A dermatoscopic image of a skin lesion; imaged for a research study, with no referral diagnosis recorded; few moles overall by the patient's own estimate; by self-report, no sunbed use; a female patient 67 years old:
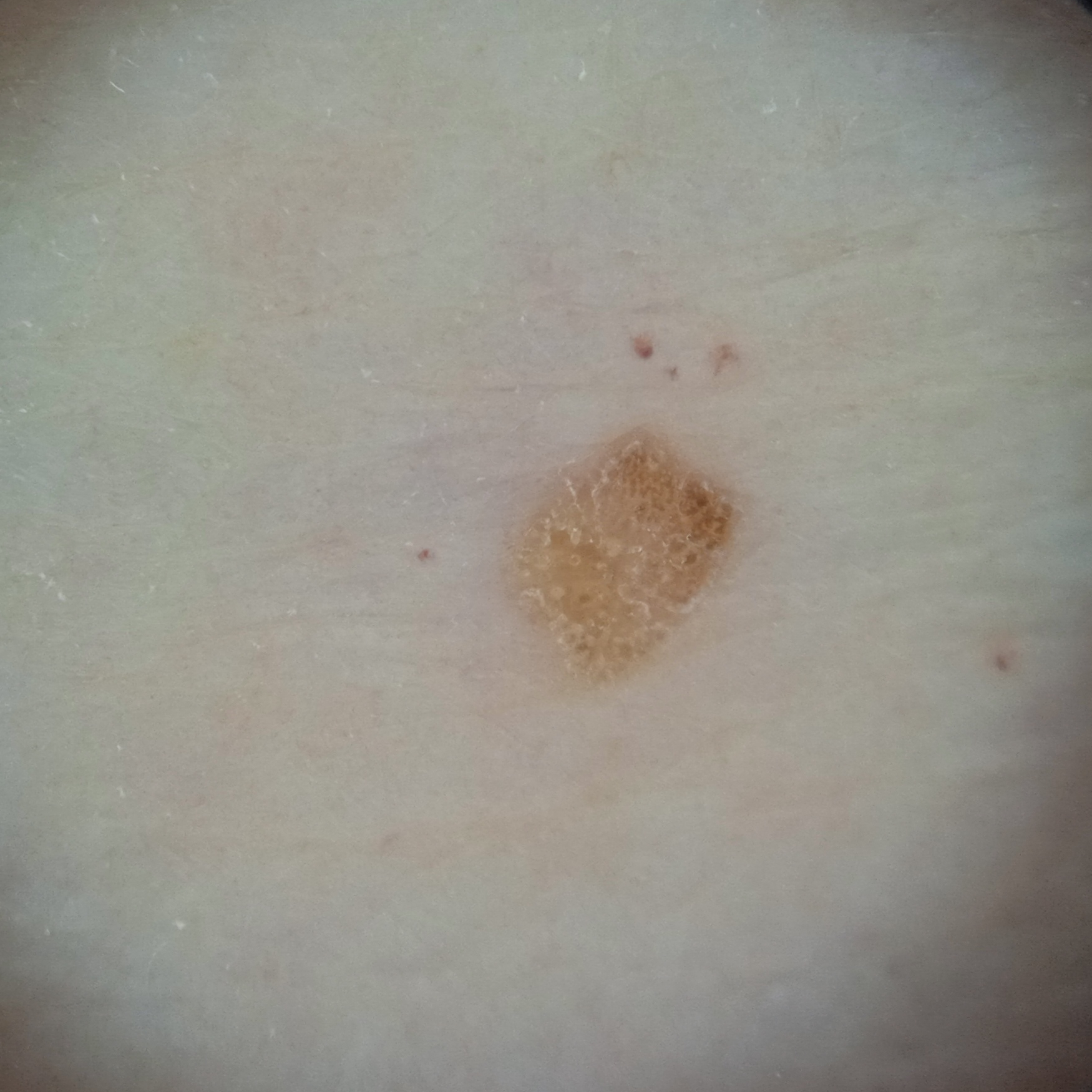site=an arm
diameter=3.1 mm
diagnostic label=seborrheic keratosis (dermatologist consensus)